The photograph was taken at a distance · located on the head or neck — 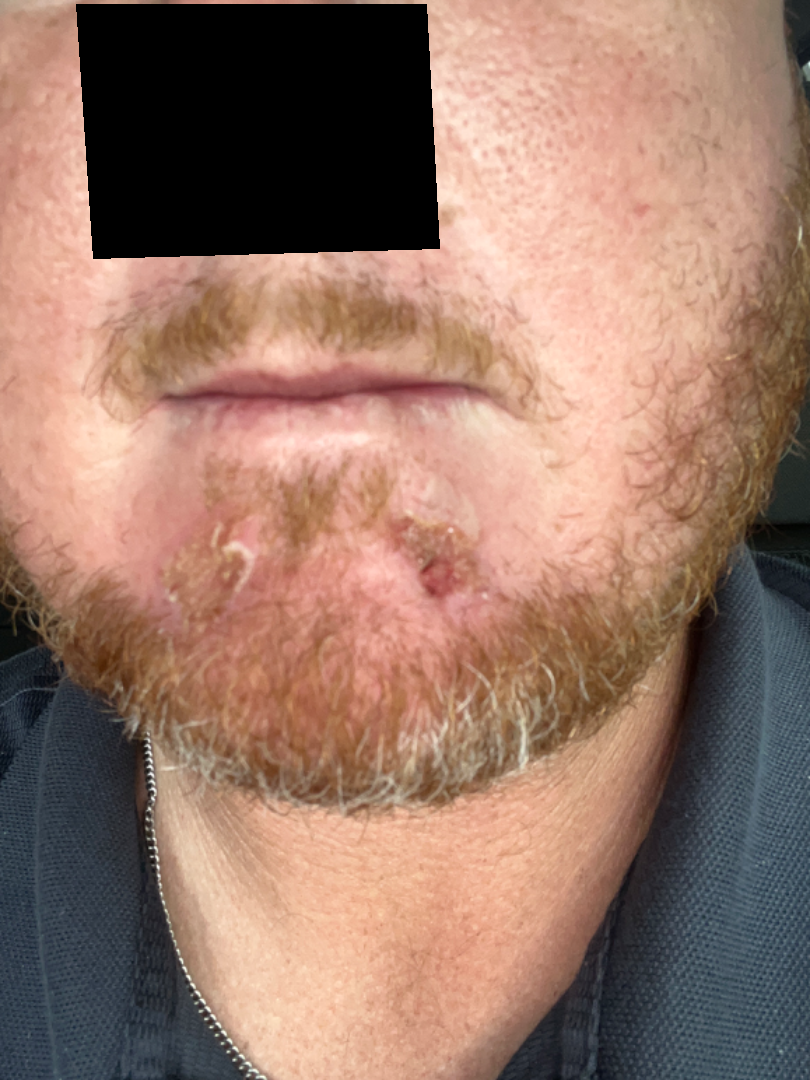The contributor notes pain and itching.
The condition has been present for less than one week.
The contributor notes the lesion is fluid-filled.
Impetigo (leading); Infected eczema (possible); Seborrheic Dermatitis (less likely).